A dermoscopic view of a skin lesion · a male patient roughly 50 years of age: 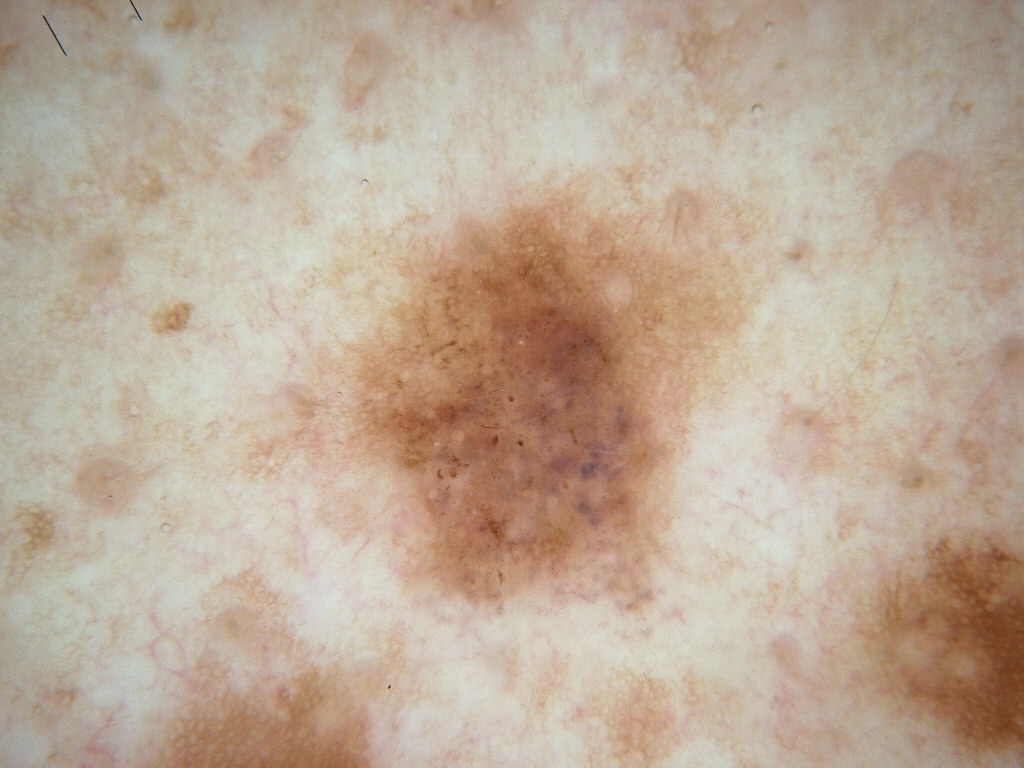In (x1, y1, x2, y2) order, lesion location: 348, 191, 740, 601. A mid-sized lesion within the field. On dermoscopy, the lesion shows milia-like cysts, pigment network, and globules; no negative network or streaks. The lesion was assessed as a melanocytic nevus, a benign lesion.